A dermoscopic image of a skin lesion.
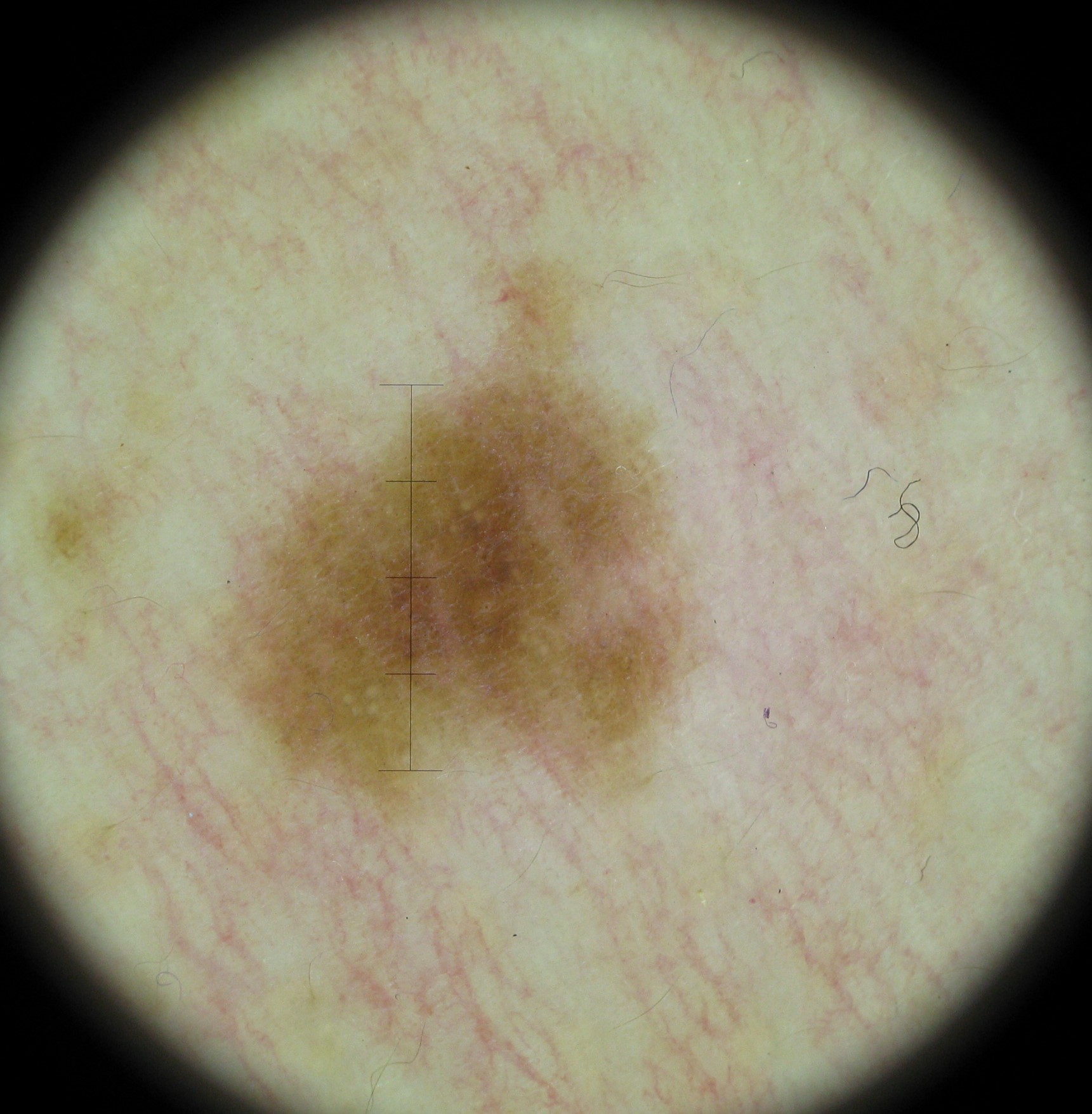Labeled as a dysplastic junctional nevus.